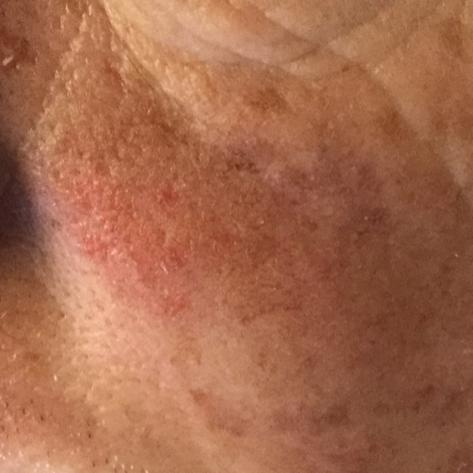A clinical photograph showing a skin lesion.
The lesion involves the face.
The patient reports that the lesion itches and has bled, but is not elevated.
The diagnostic impression was a lesion of indeterminate malignant potential — an actinic keratosis.